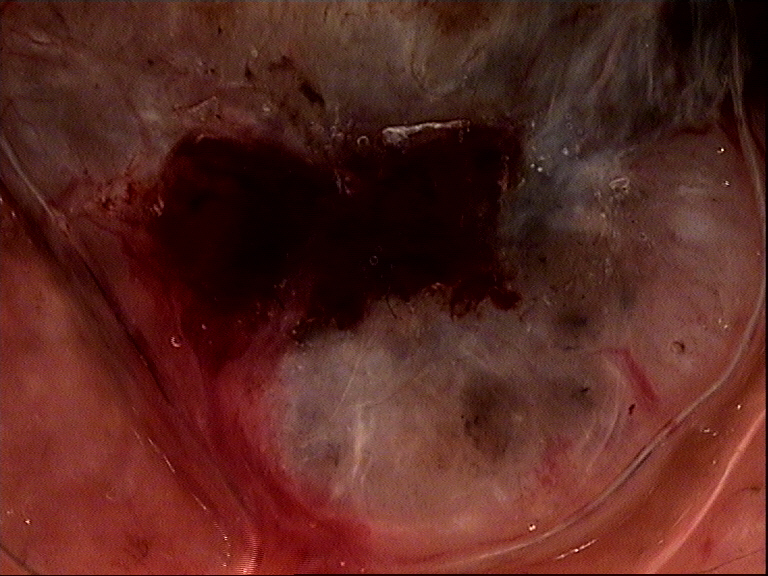The biopsy diagnosis was a basal cell carcinoma.